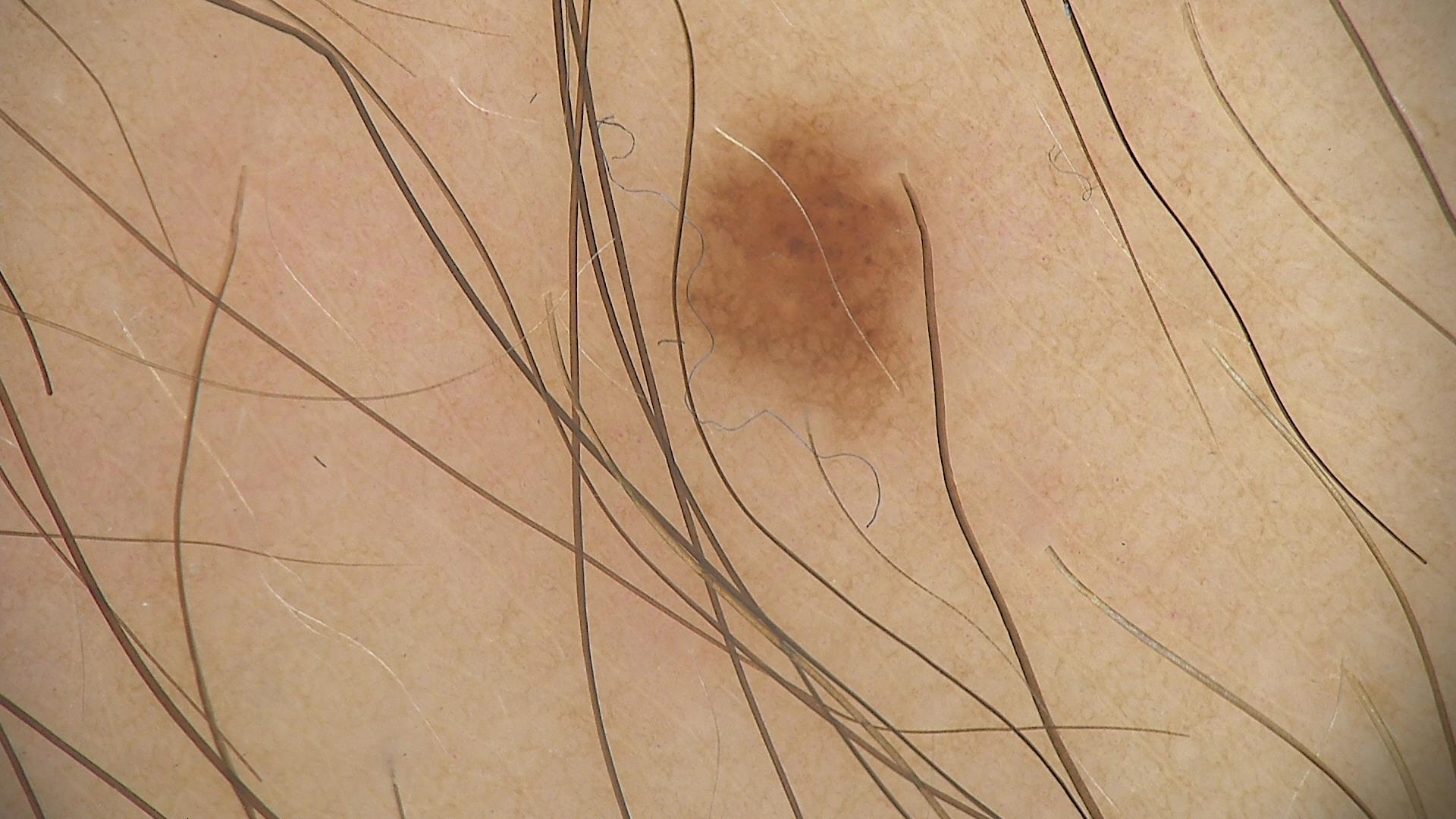A dermoscopic photograph of a skin lesion. Classified as a dysplastic junctional nevus.